Reported duration is about one day. Texture is reported as raised or bumpy. The photograph was taken at a distance. Self-categorized by the patient as a rash. The contributor is a male aged 18–29. Self-reported Fitzpatrick IV: 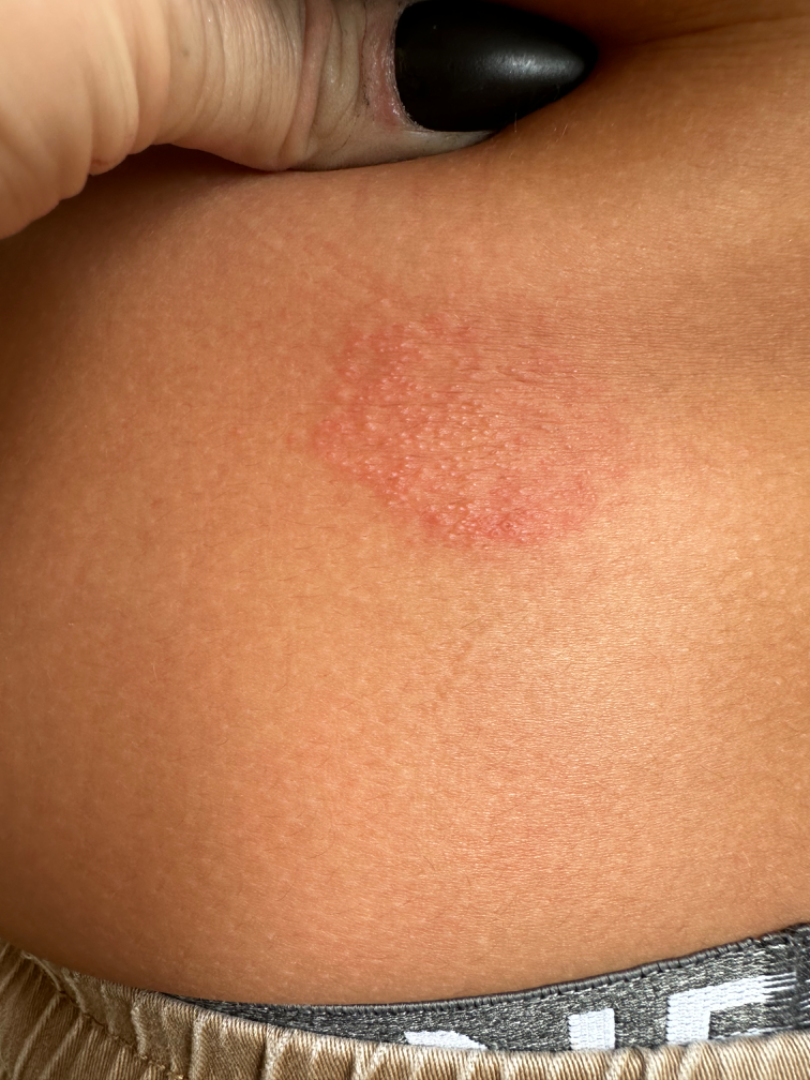differential: Eczema